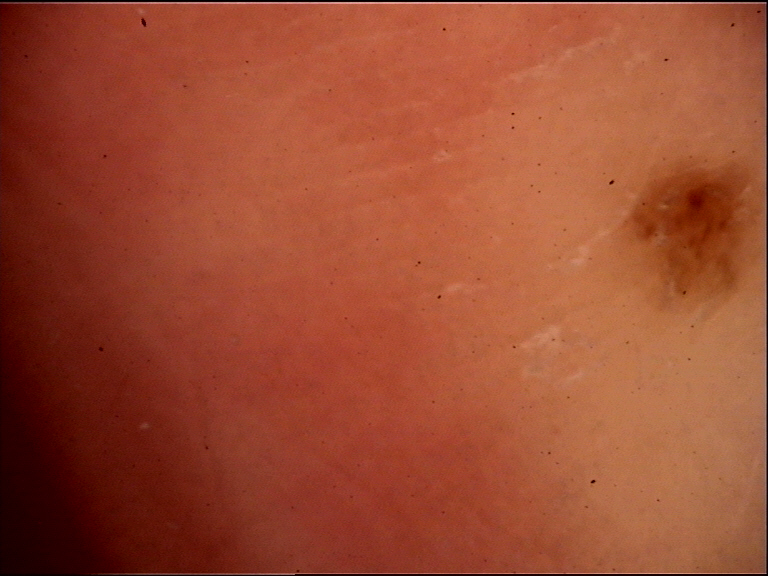Q: What kind of image is this?
A: dermoscopy
Q: What is the diagnosis?
A: acral junctional nevus (expert consensus)